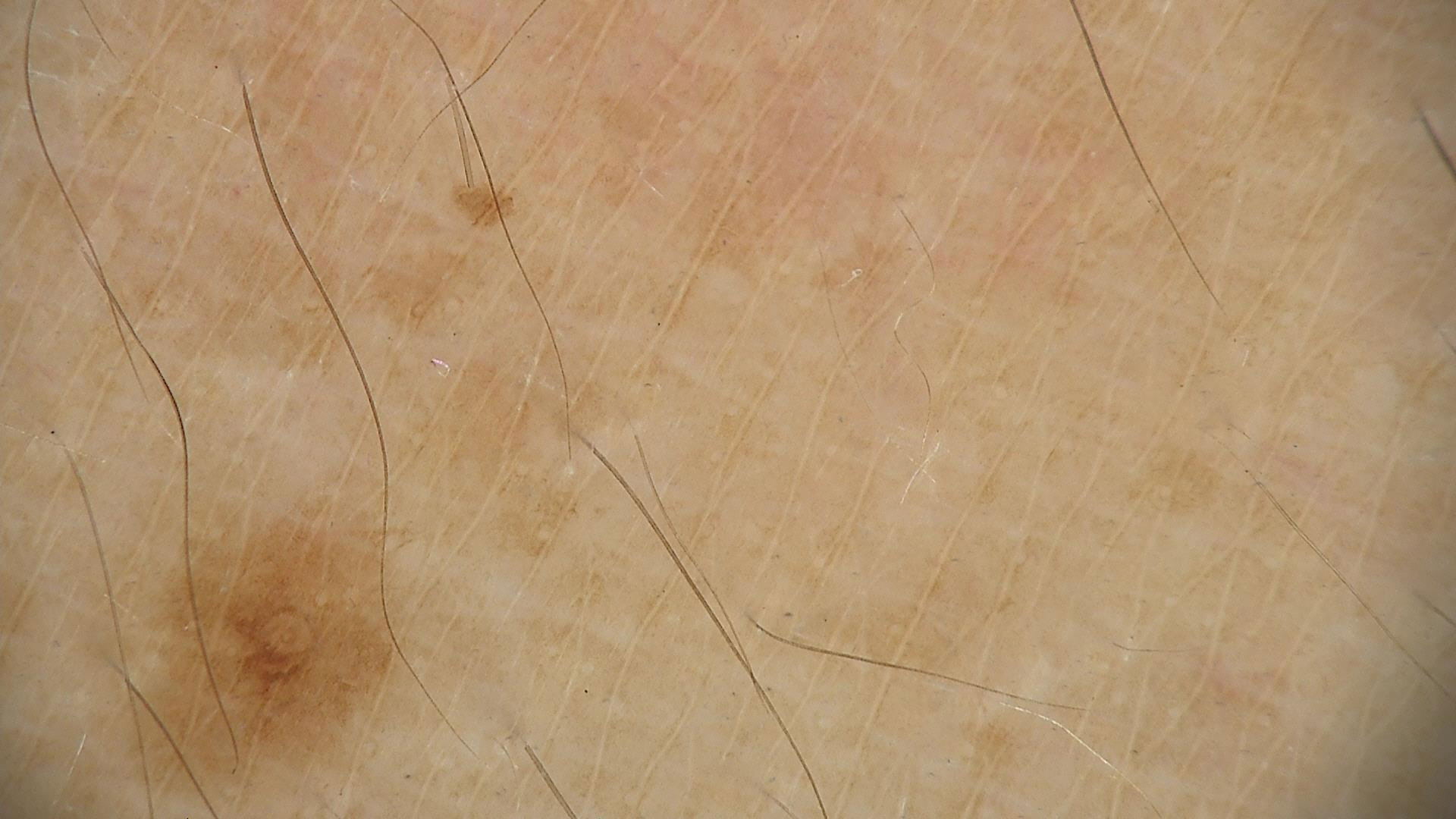class = junctional nevus (expert consensus).